The patient says their skin reddens painfully with sun exposure · on a questionnaire the patient reported no sunbed use and no personal history of skin cancer · acquired for a research image collection, with no referral diagnosis · a moderate number of moles by the patient's own estimate · a dermoscopic image of a skin lesion · a female patient aged 81:
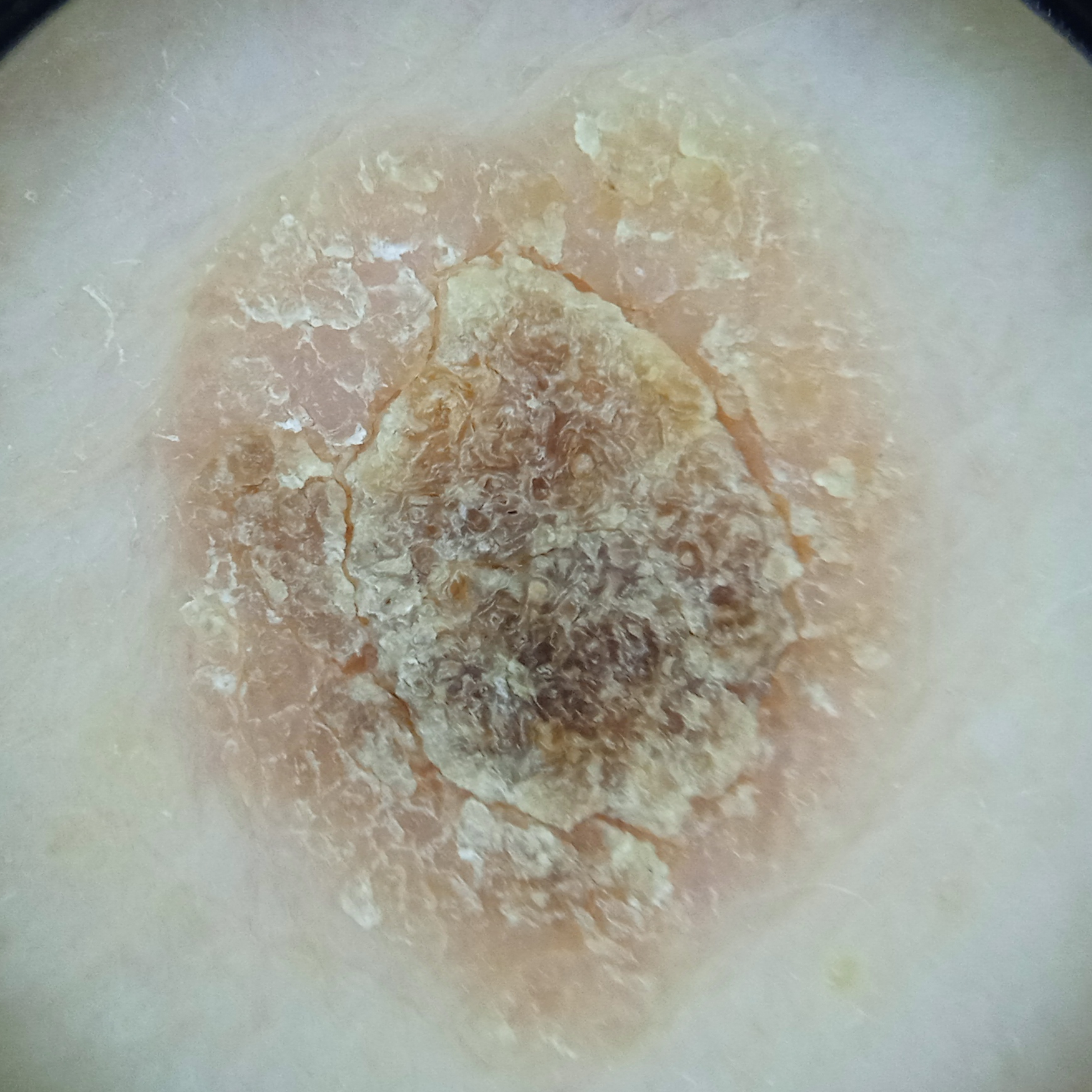Q: What is the anatomic site?
A: the back
Q: Lesion size?
A: 9.8 mm
Q: What was the diagnosis?
A: seborrheic keratosis (dermatologist consensus)